The photograph was taken at a distance · the leg is involved:
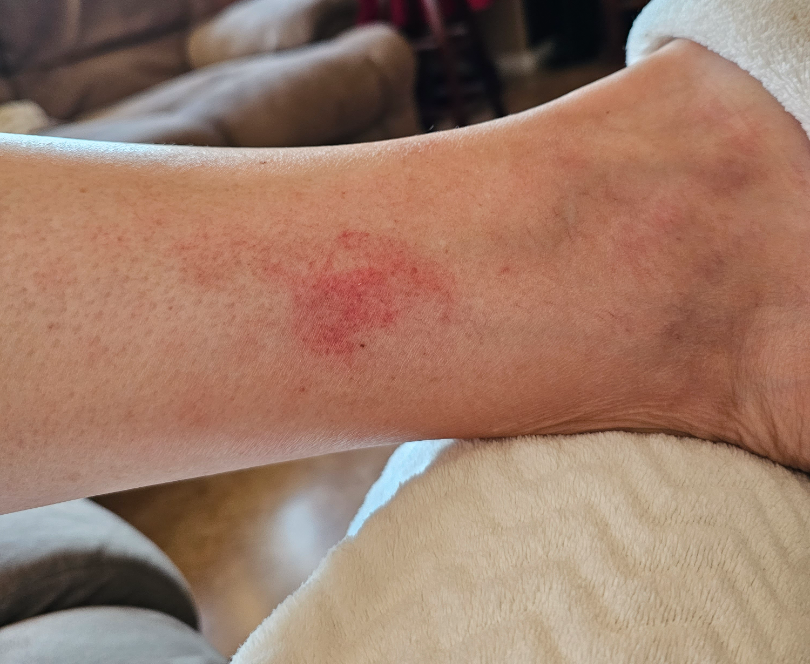assessment = could not be assessed, described texture = flat, symptoms = none reported, onset = about one day, constitutional symptoms = none reported.